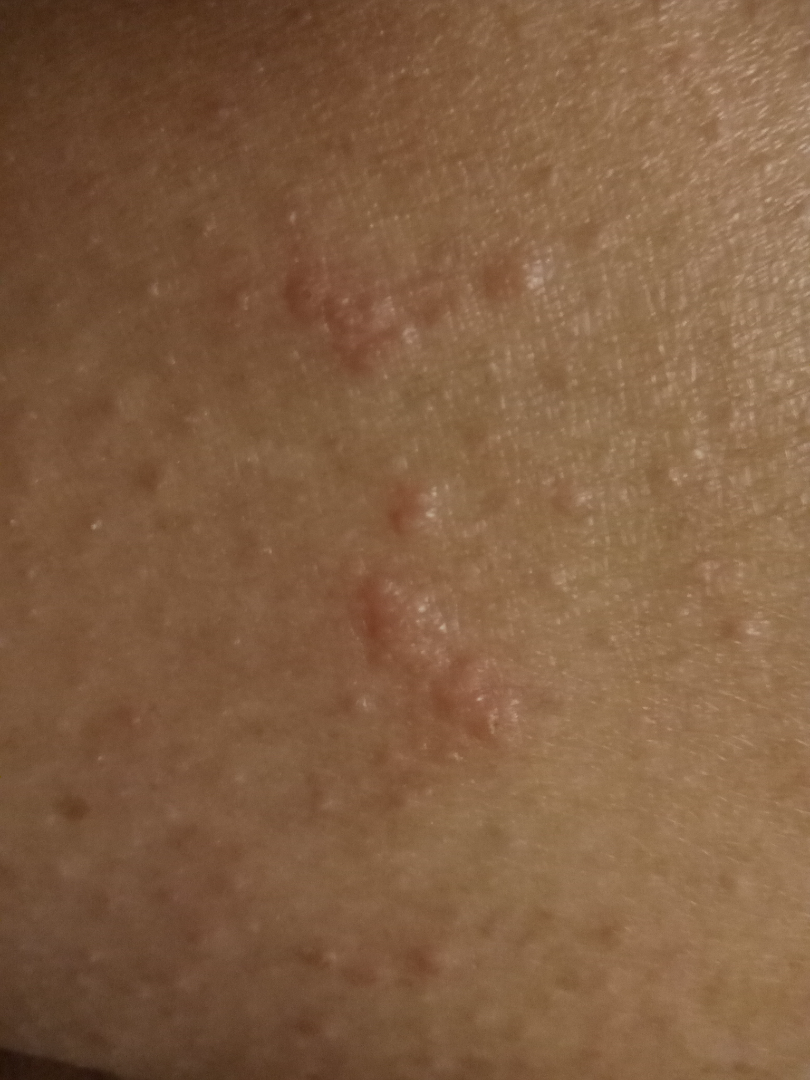assessment: the differential is split between Insect Bite and Allergic Contact Dermatitis; an alternative is Herpes Zoster